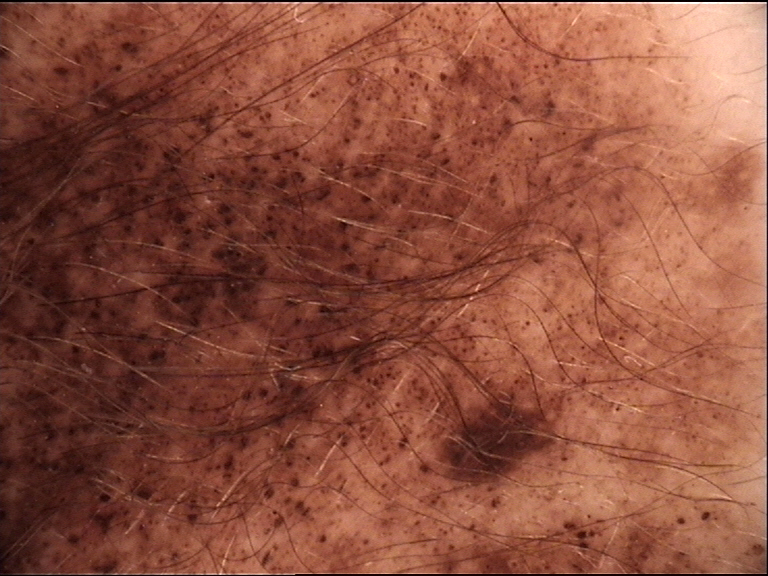Findings: A dermoscopic photograph of a skin lesion. The morphology is that of a banal lesion. Conclusion: Classified as a congenital compound nevus.